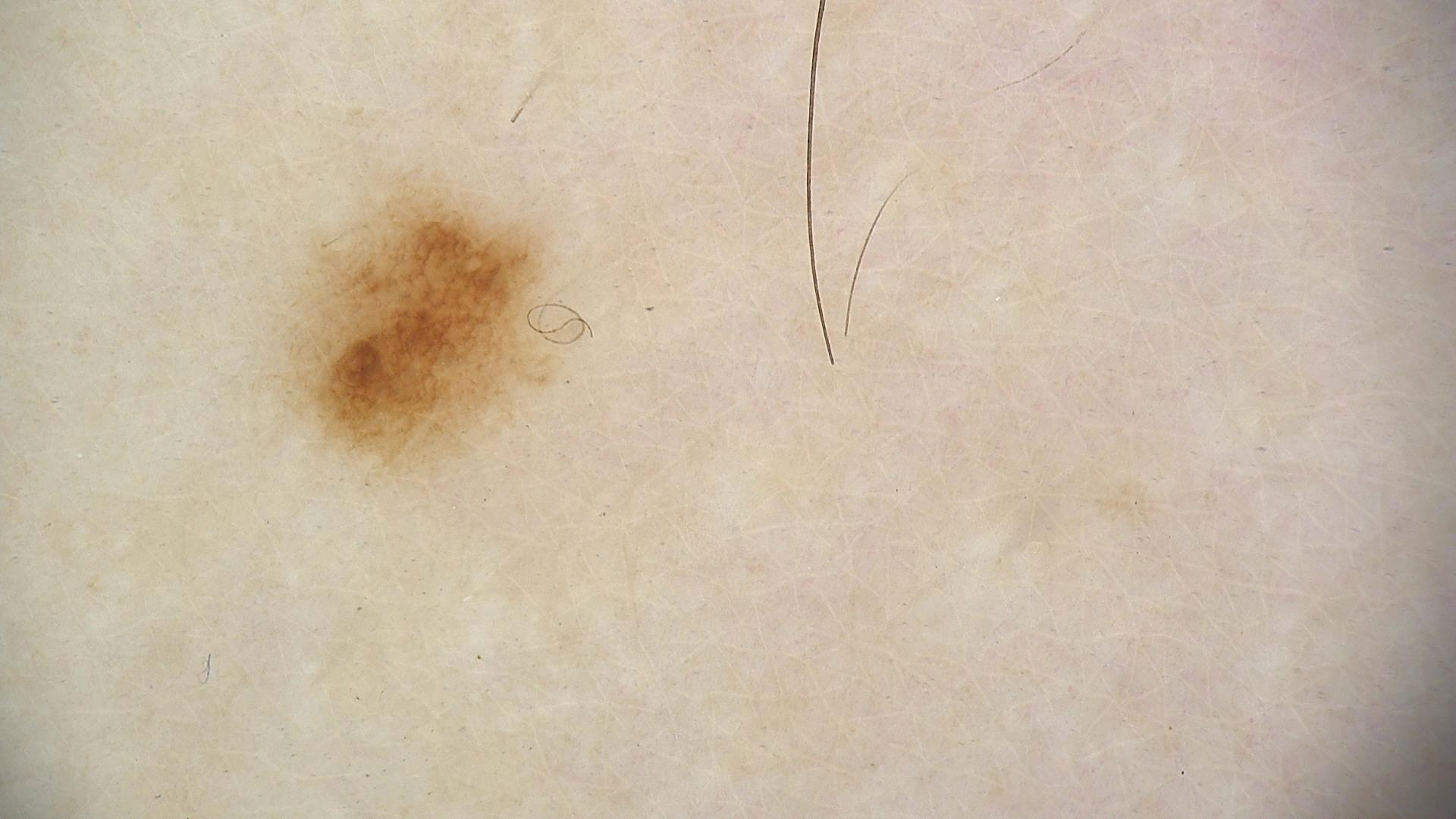Q: What kind of image is this?
A: dermoscopy
Q: What is this lesion?
A: dysplastic junctional nevus (expert consensus)